Fitzpatrick III; lay graders estimated 3 on the MST, this image was taken at an angle — 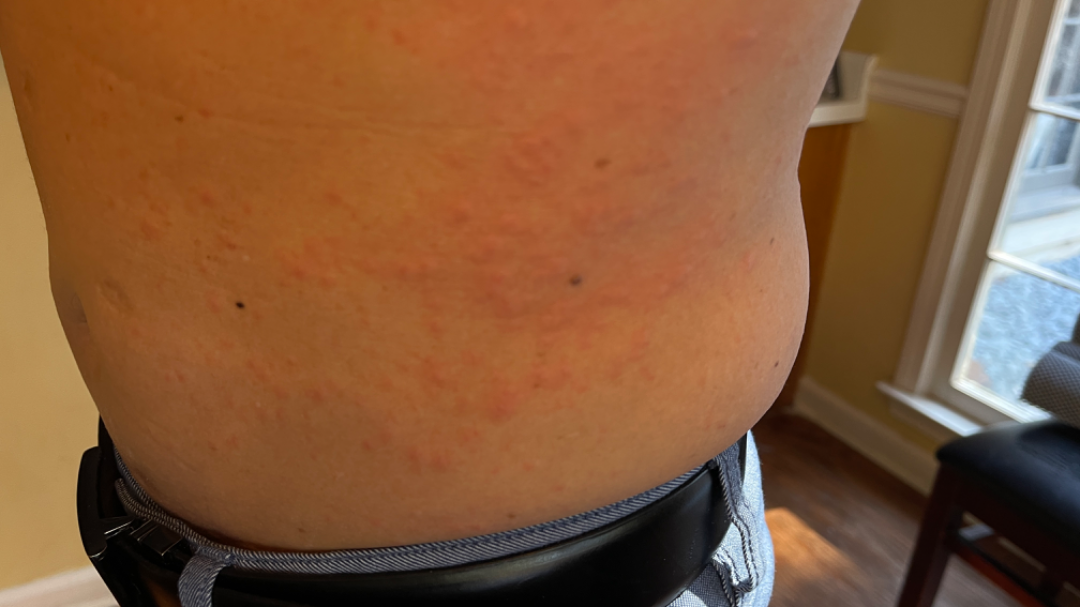Review:
The reviewing clinician's impression was: most consistent with Urticaria.